A dermatoscopic image of a skin lesion.
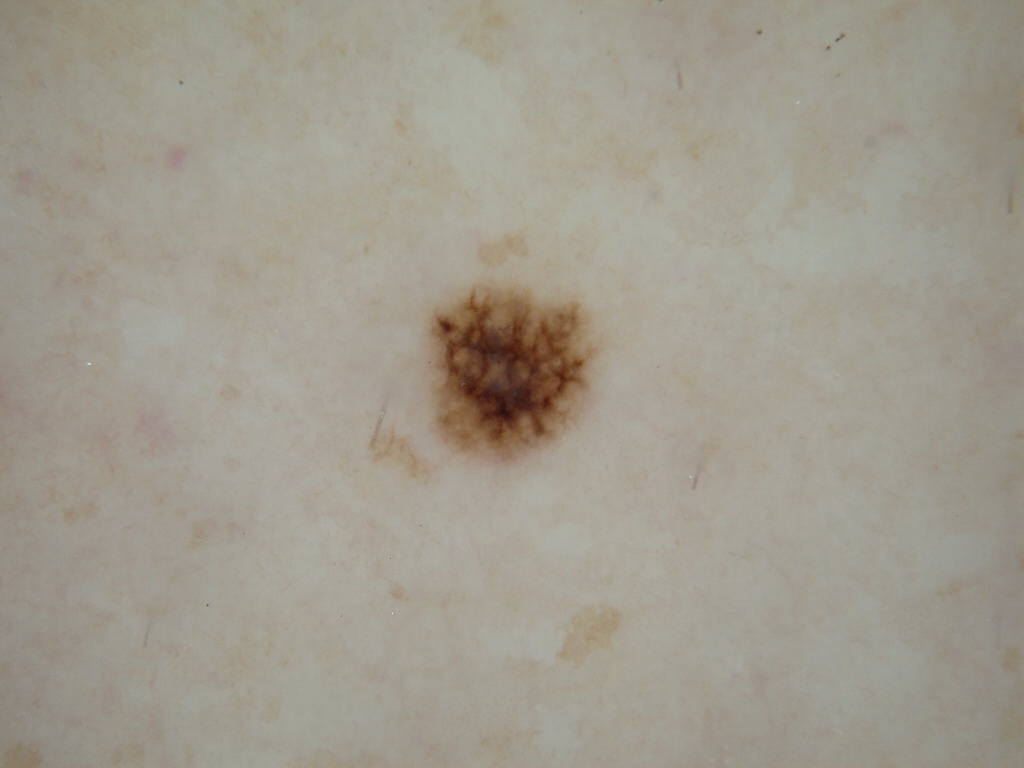dermoscopic features not present = negative network, pigment network, globules, milia-like cysts, and streaks | lesion location = x1=425, y1=279, x2=599, y2=463 | lesion size = small | impression = a melanocytic nevus.